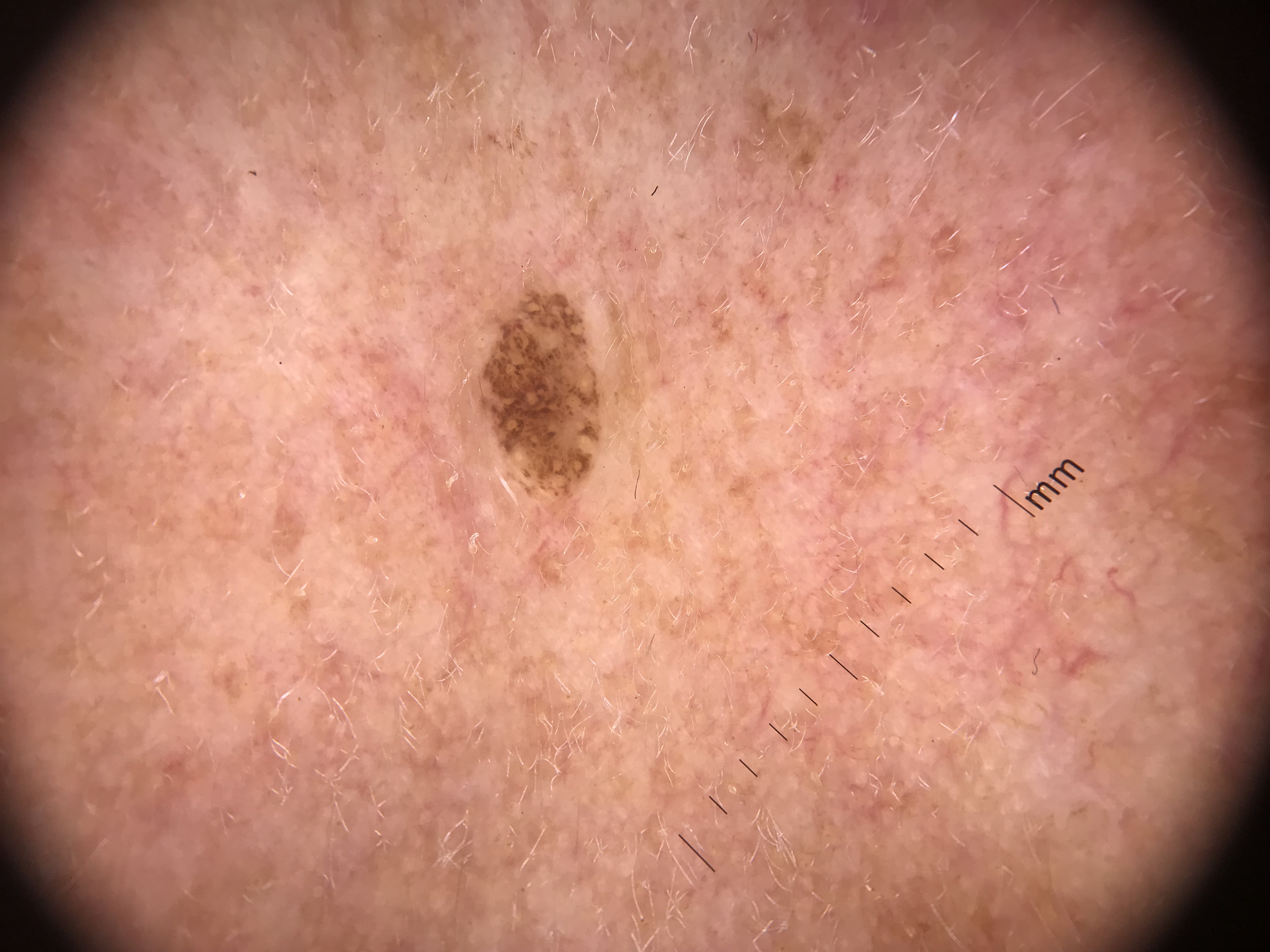Findings: A dermoscopic close-up of a skin lesion. The architecture is that of a banal lesion. Impression: The diagnosis was a compound nevus.